Imaged for a research study, with no referral diagnosis recorded; the patient describes having numerous moles; a clinical photograph of a skin lesion; a female patient 26 years old; by self-report, a history of sunbed use and no personal history of cancer; the patient says their skin reddens with sun exposure — 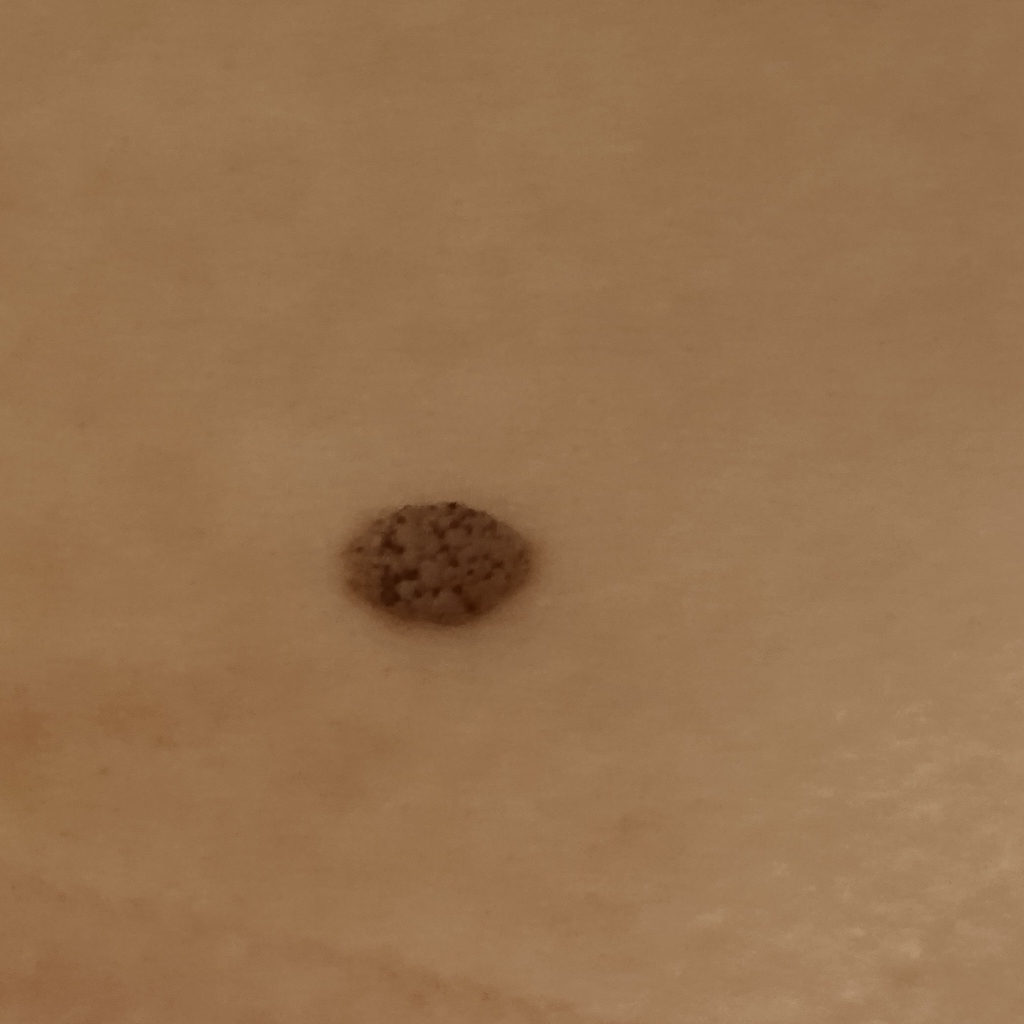anatomic site = the back
size = 8.4 mm
diagnosis = seborrheic keratosis (dermatologist consensus)